The photograph is a close-up of the affected area — 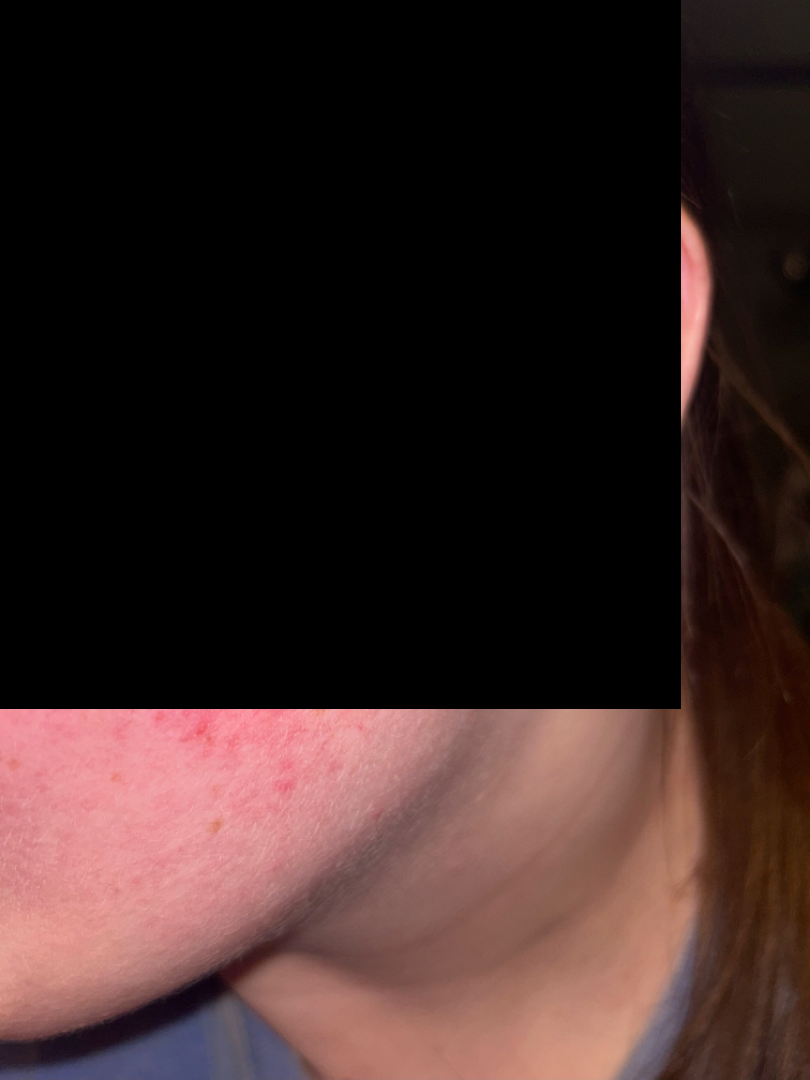assessment = one reviewing dermatologist: most likely Rosacea; possibly Acne; also raised was Allergic Contact Dermatitis